The lesion involves the arm, close-up view: 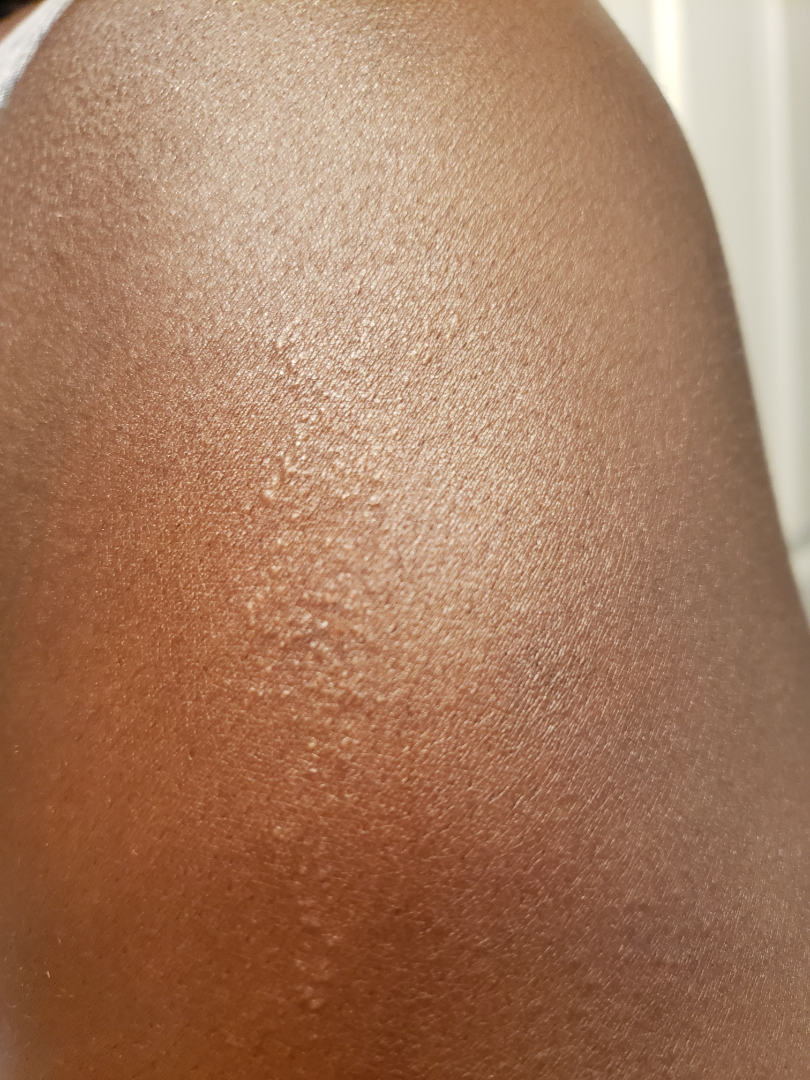Review: Eczema and Lichen striatus were each considered, in no particular order.